The arm is involved · the photo was captured at an angle · female subject, age 40–49:
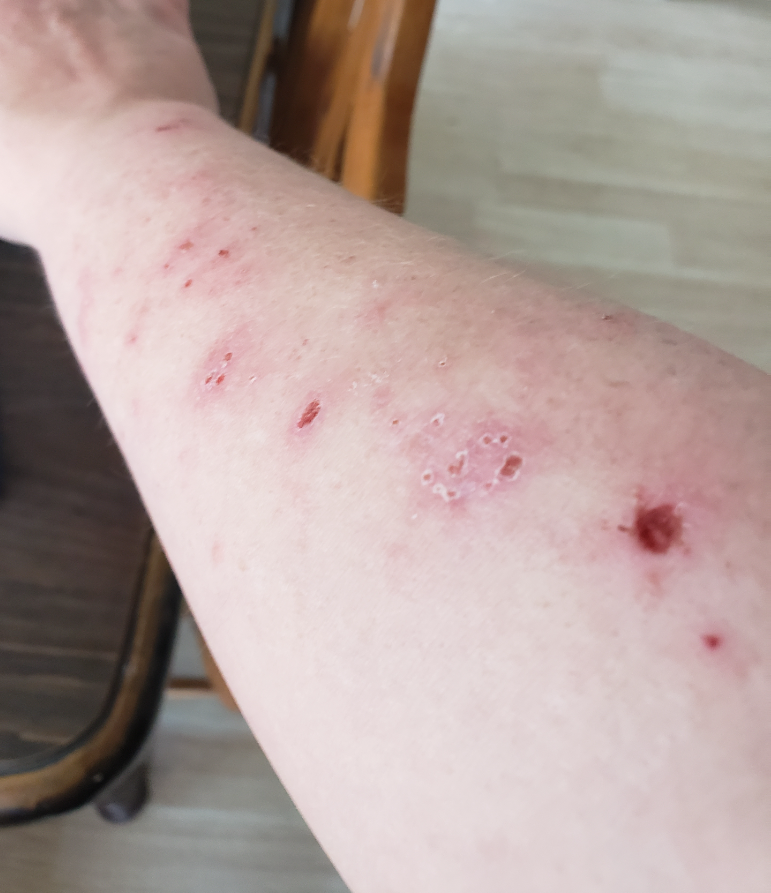Findings:
– clinical impression: most consistent with Eczema; an alternative is Allergic Contact Dermatitis; less likely is Psoriasis